A skin lesion imaged with a dermatoscope:
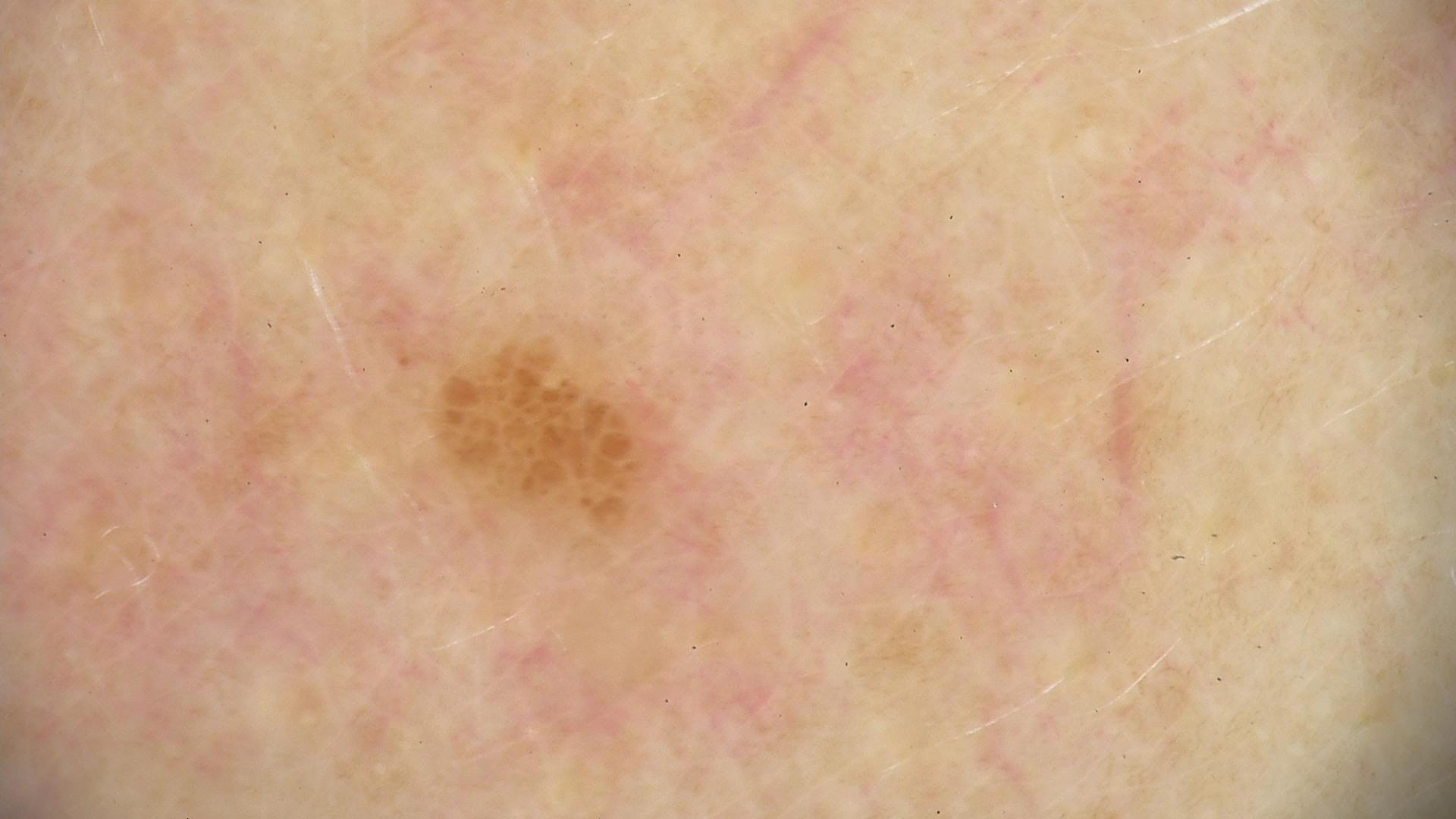Consistent with a benign lesion — a dysplastic junctional nevus.